A dermoscopic photograph of a skin lesion.
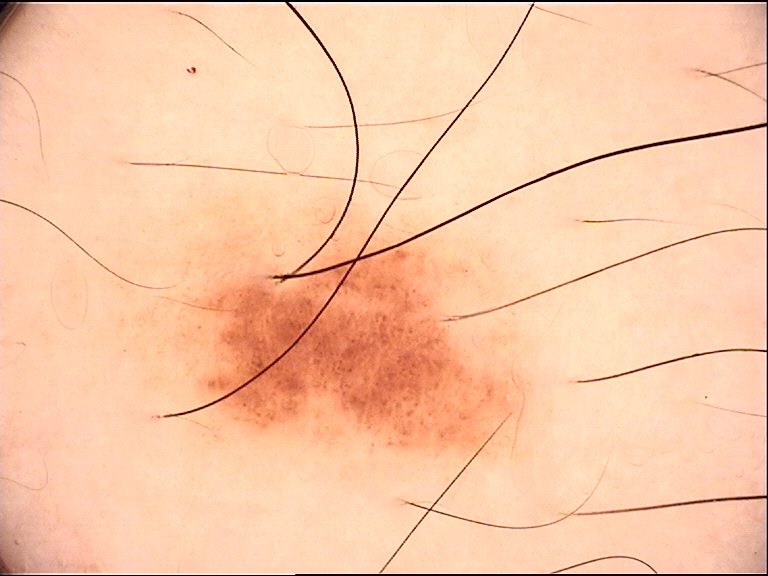Classified as a benign lesion — a dysplastic junctional nevus.